The photo was captured at an angle; human graders estimated Monk Skin Tone 3–4: 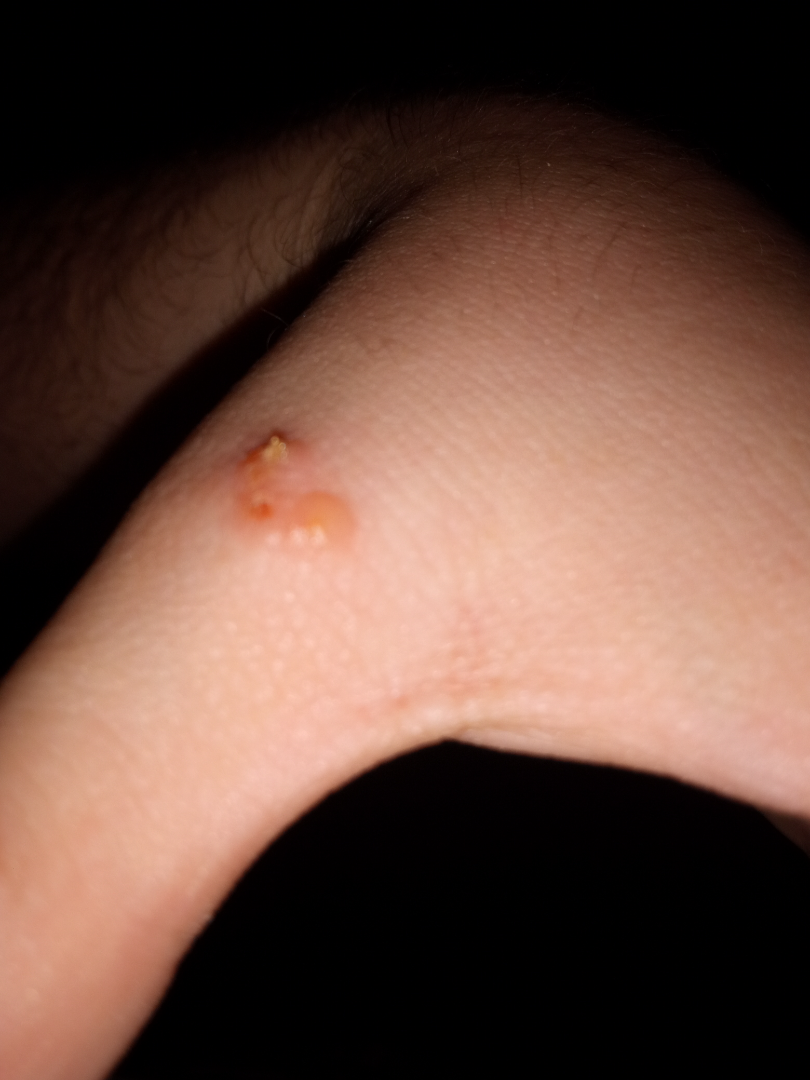The reviewing clinician's impression was: Impetigo (33%); Molluscum Contagiosum (33%); Herpes Simplex (33%).